The patient considered this a rash; close-up view; the lesion is associated with itching; male subject, age 18–29; the affected area is the arm — 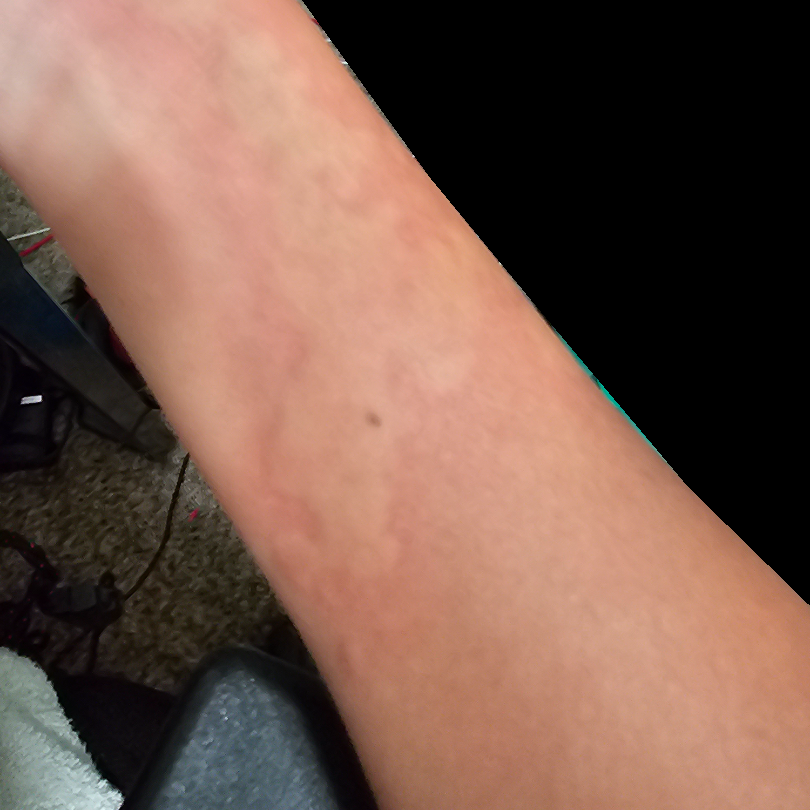differential diagnosis: the reviewer's impression was Urticaria.